A dermoscopic image of a skin lesion: 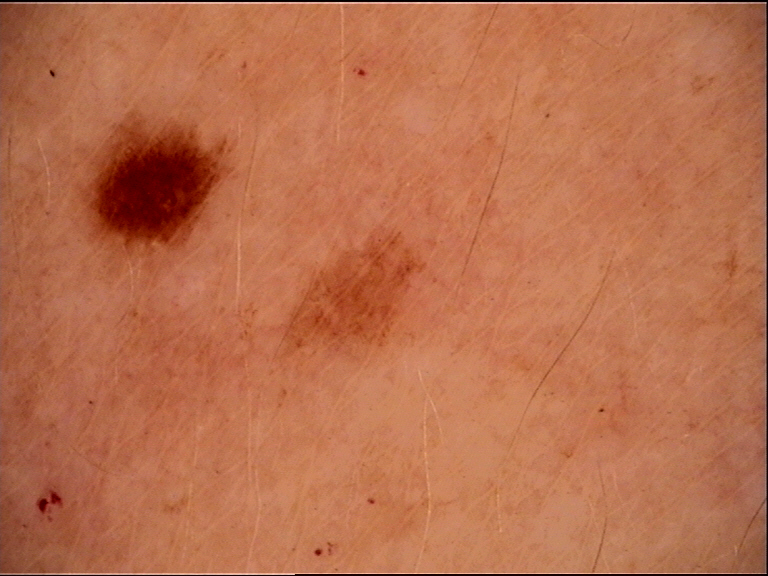Impression:
The diagnostic label was a benign lesion — a dysplastic junctional nevus.